Collected as part of a research study, without a referral diagnosis; the patient says their skin tans without first burning; by self-report, a personal history of skin cancer and a personal history of cancer; few moles overall by the patient's own estimate; a skin lesion imaged with a dermatoscope:
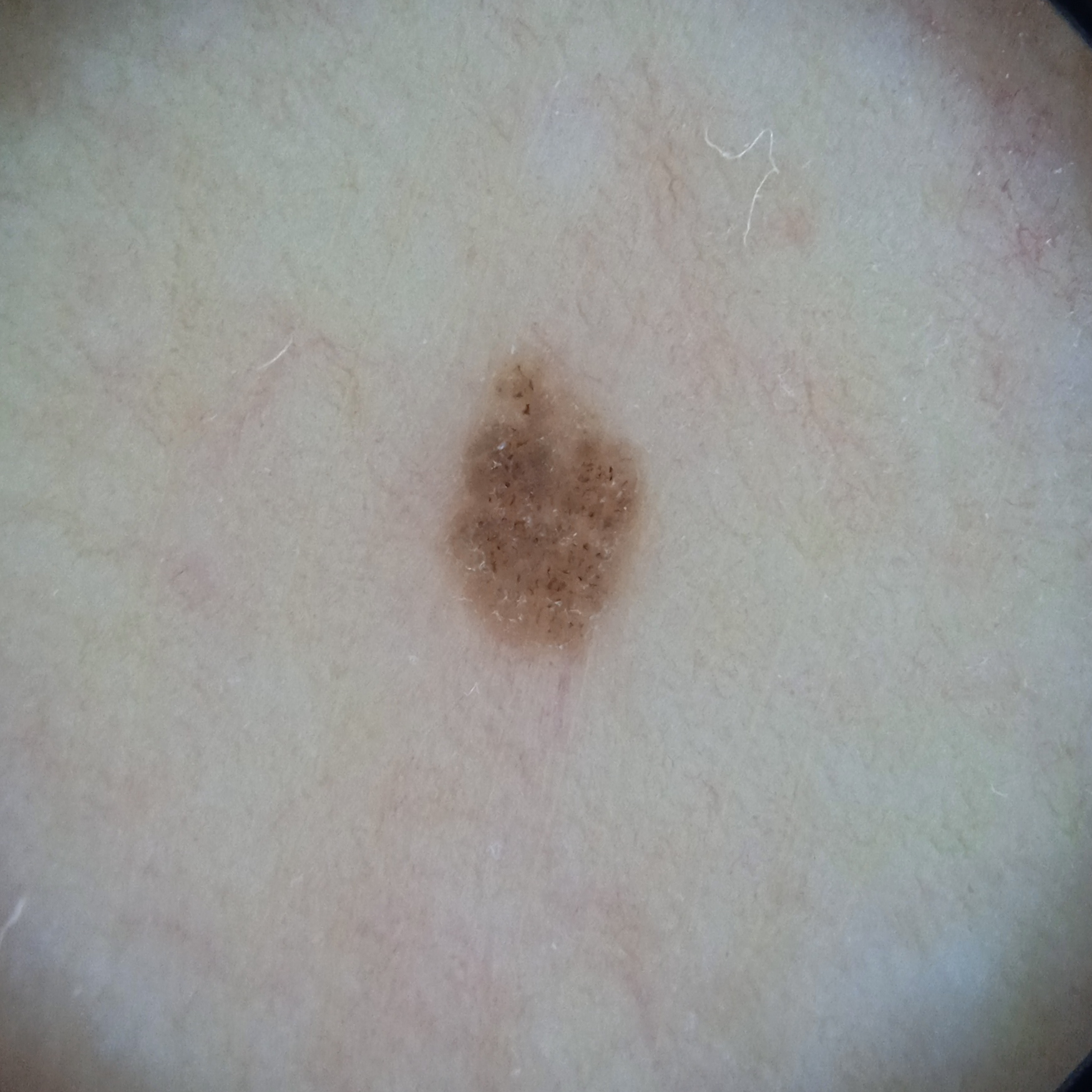The lesion is on the torso. The lesion measures approximately 3.4 mm. The diagnostic impression was a melanocytic nevus.